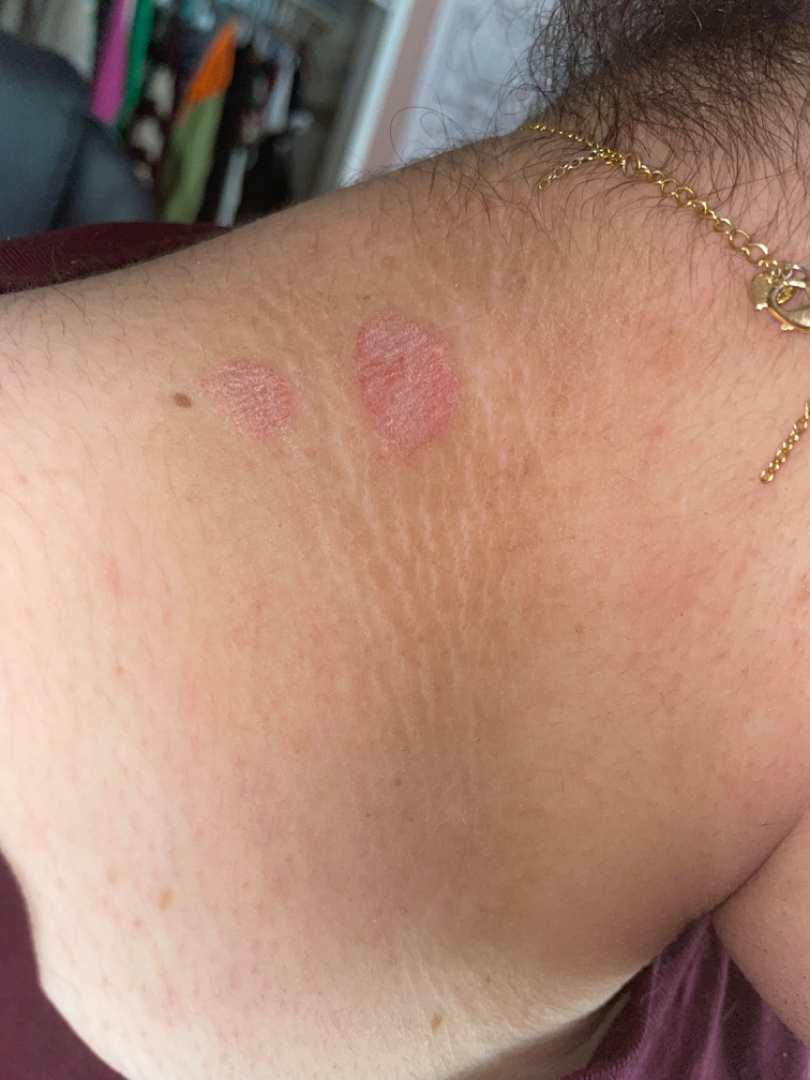Reported duration is one to four weeks.
No relevant systemic symptoms.
The contributor notes the lesion is raised or bumpy.
The affected area is the head or neck.
A close-up photograph.
The leading consideration is Psoriasis; an alternative is Eczema; less probable is Tinea.